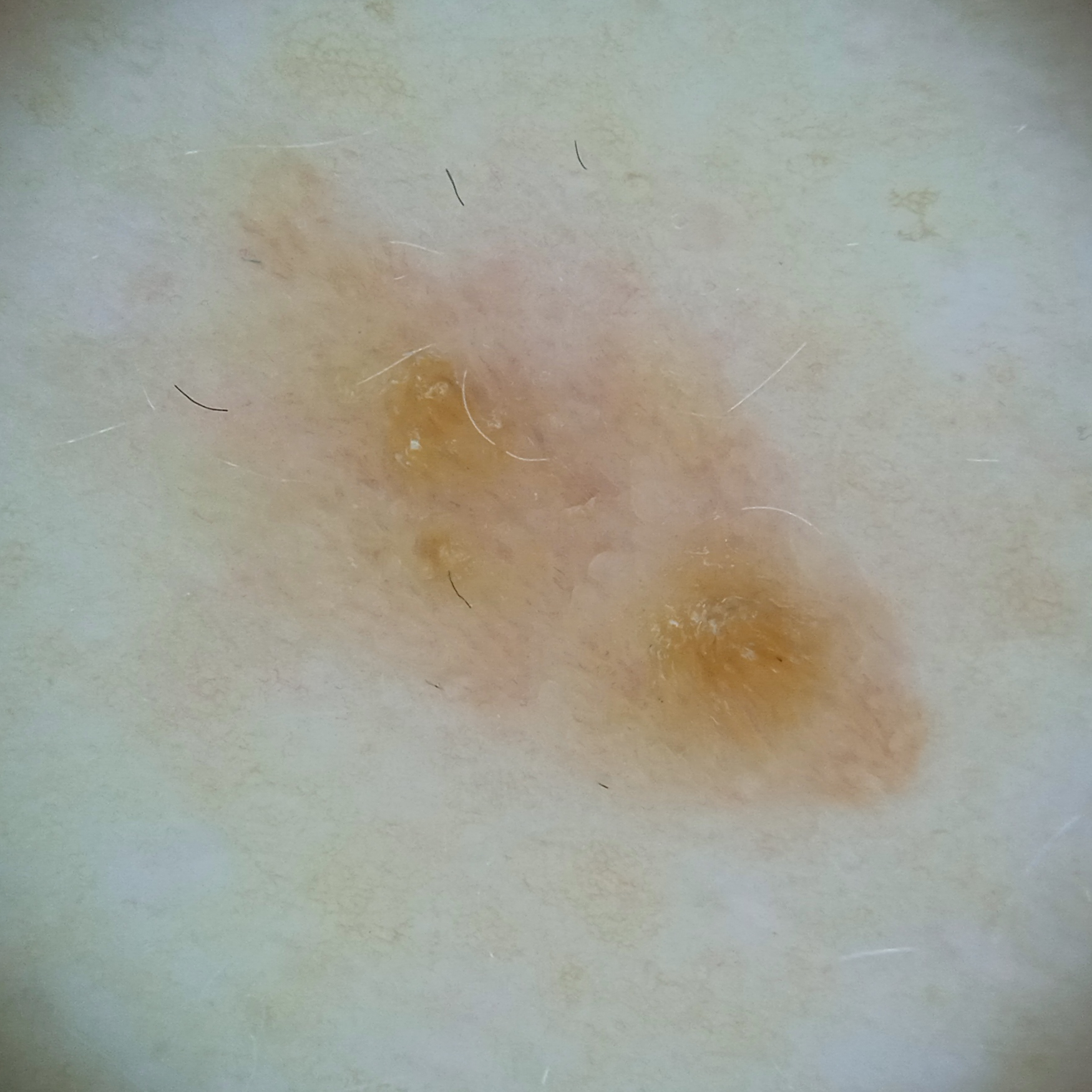Case:
• patient — female, aged 59
• sun reaction — skin reddens with sun exposure
• clinical context — research study (no referral diagnosis)
• imaging — dermoscopy
• body site — the torso
• diameter — 9.1 mm
• assessment — seborrheic keratosis (dermatologist consensus)